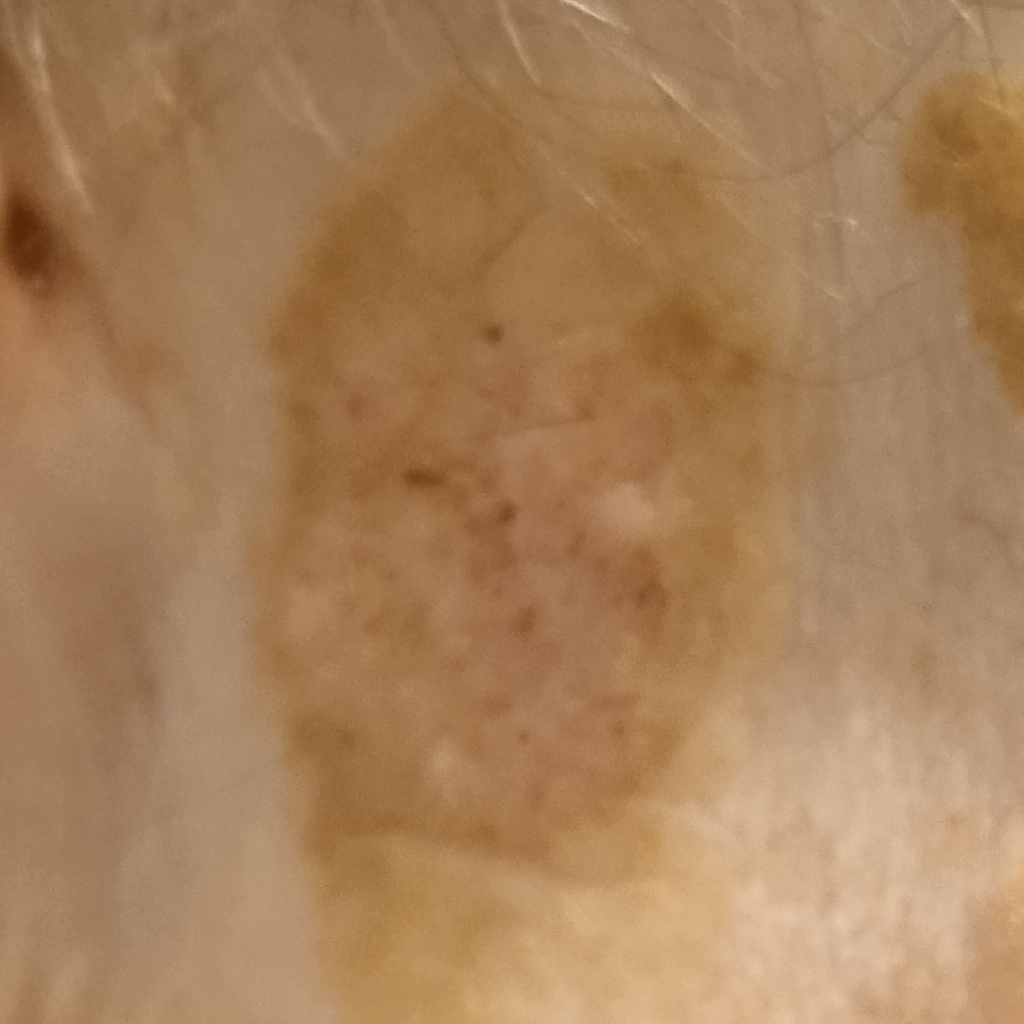Case summary: A female patient aged 81. A clinical photograph showing a skin lesion. The patient says their skin reddens painfully with sun exposure. A moderate number of moles by the patient's own estimate. The lesion measures approximately 36.6 mm. Conclusion: The diagnostic impression was a seborrheic keratosis.